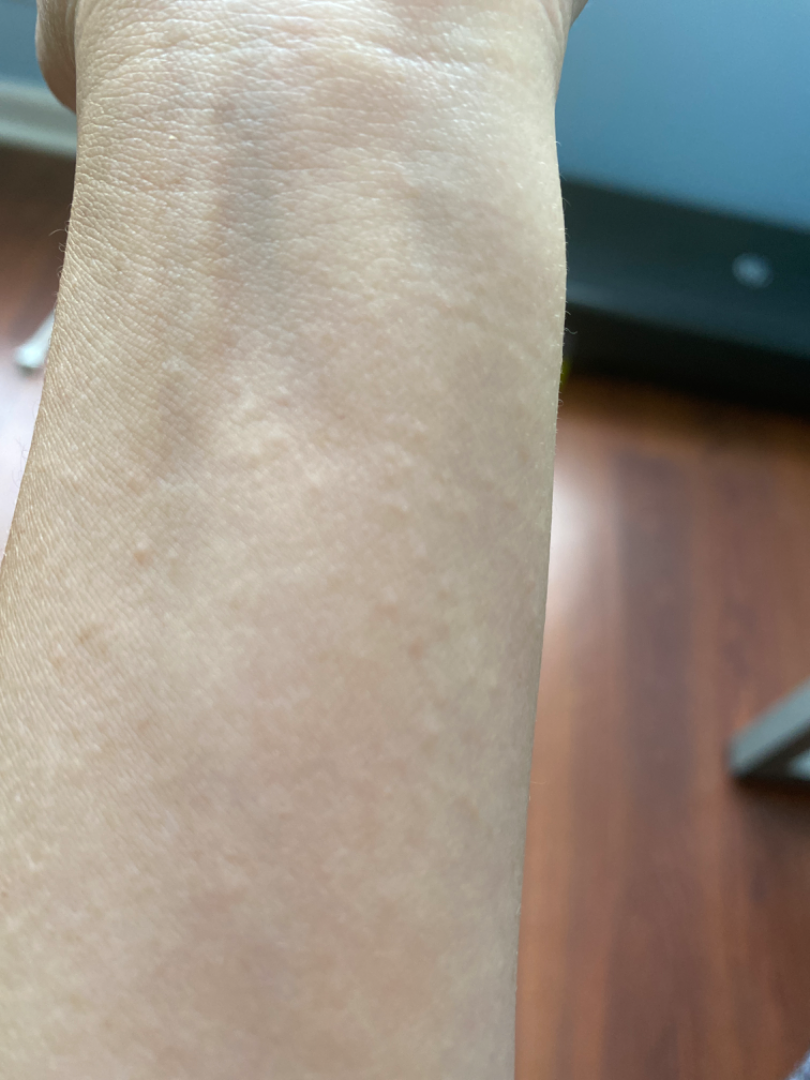assessment: unable to determine | history: about one day | symptoms: none reported | body site: arm | skin tone: Fitzpatrick phototype III; lay graders estimated 1 on the Monk skin tone scale | image framing: close-up | described texture: raised or bumpy | patient's own categorization: a rash | associated systemic symptoms: none reported.